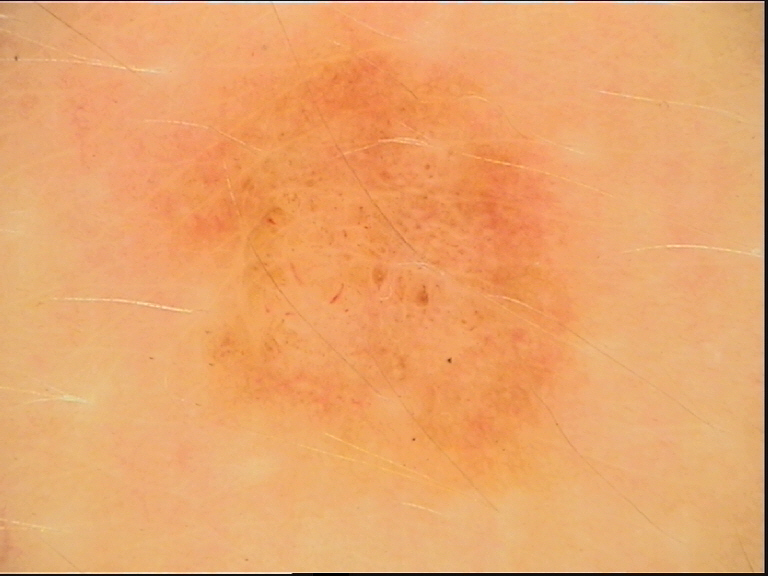Diagnosed as a dysplastic junctional nevus.